A dermoscopic image of a skin lesion.
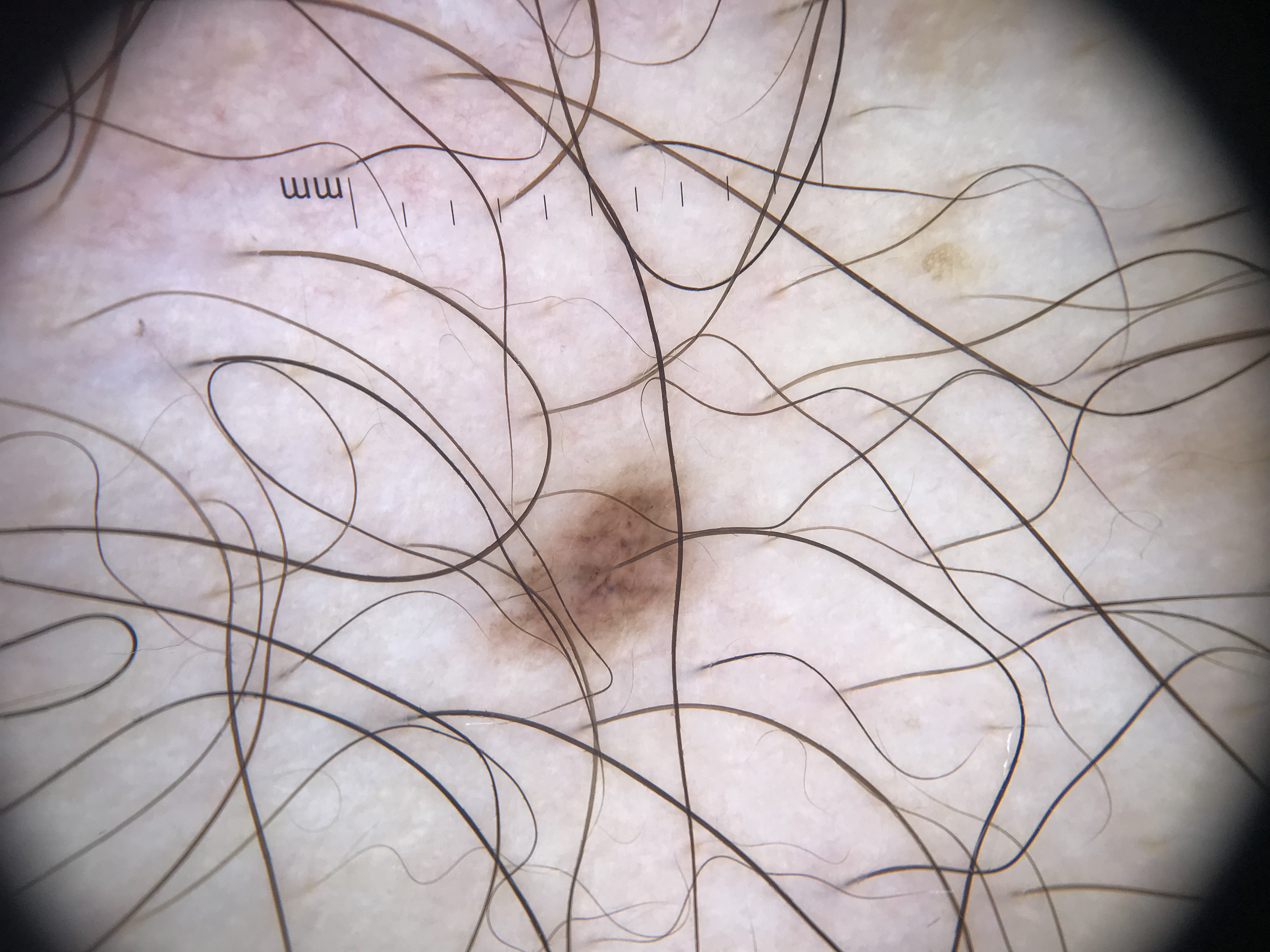Diagnosed as a dysplastic junctional nevus.